A dermoscopic image of a skin lesion.
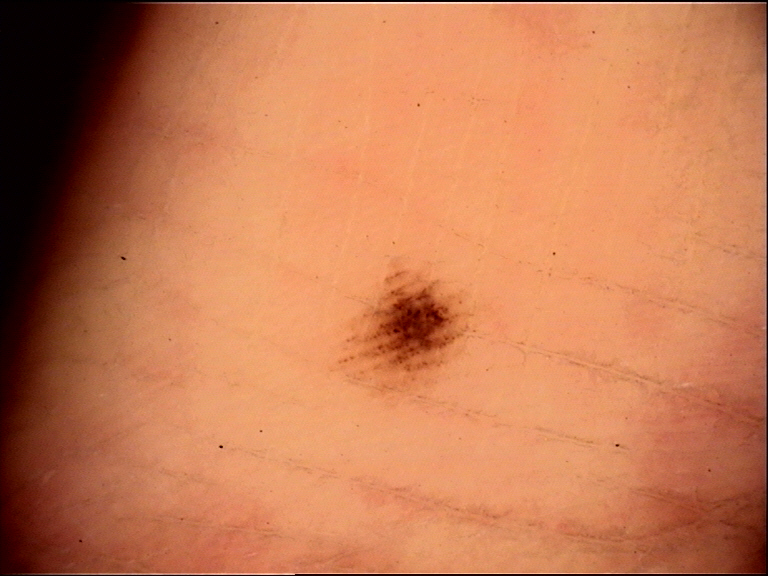<dermoscopy>
  <diagnosis>
    <name>acral dysplastic junctional nevus</name>
    <code>ajd</code>
    <malignancy>benign</malignancy>
    <super_class>melanocytic</super_class>
    <confirmation>expert consensus</confirmation>
  </diagnosis>
</dermoscopy>